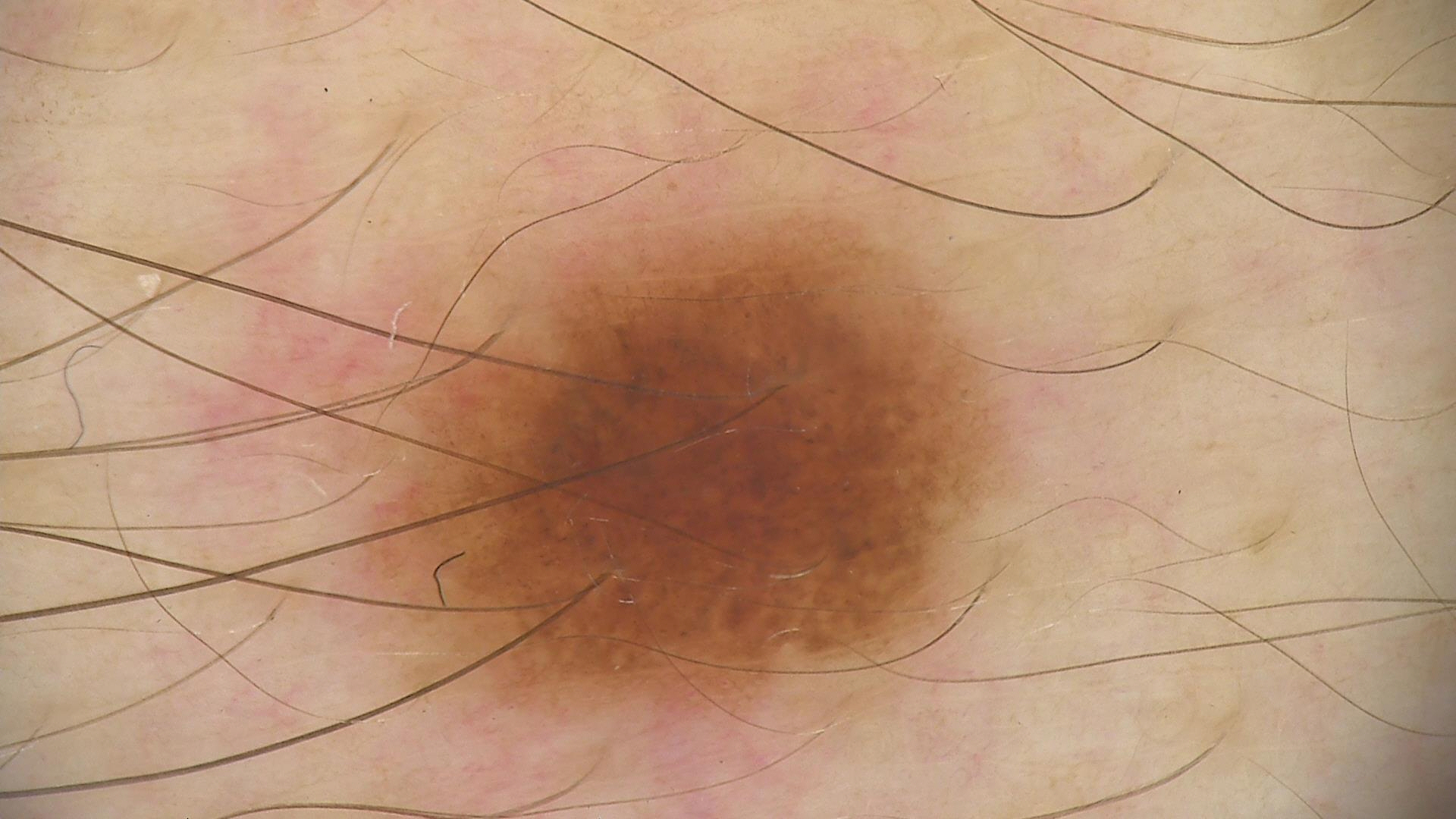Summary:
A dermoscopy image of a single skin lesion.
Impression:
Classified as a banal lesion — a compound nevus.